A skin lesion imaged with a dermatoscope.
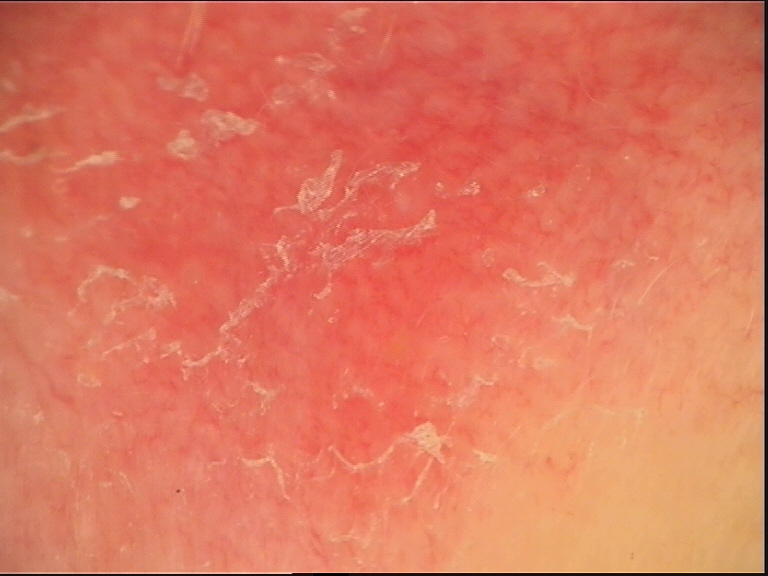label: Bowen's disease (biopsy-proven)